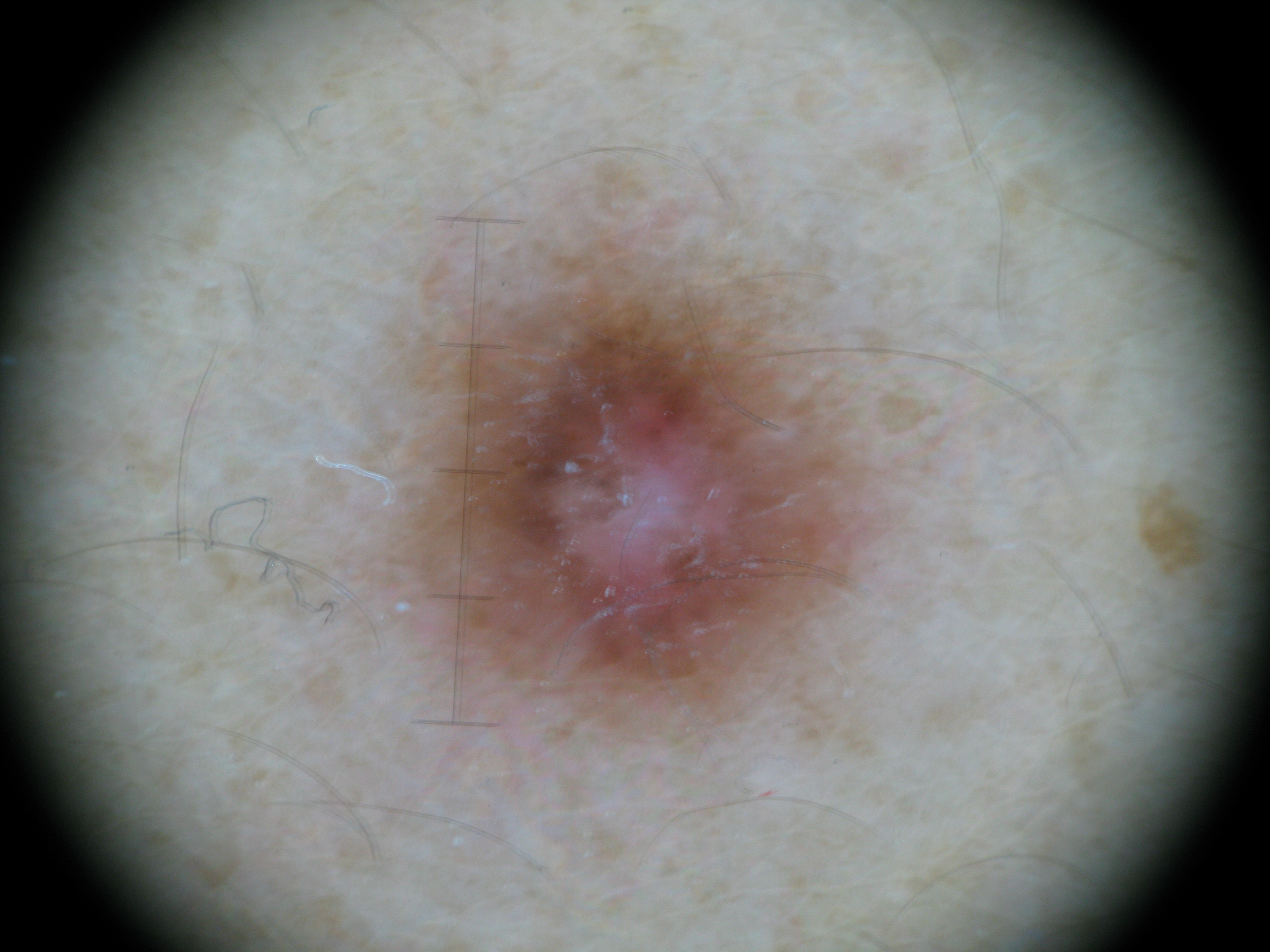{"image": "dermatoscopy", "diagnosis": {"name": "dermatofibroma", "code": "df", "malignancy": "benign", "super_class": "non-melanocytic", "confirmation": "expert consensus"}}